A dermoscopic image of a skin lesion.
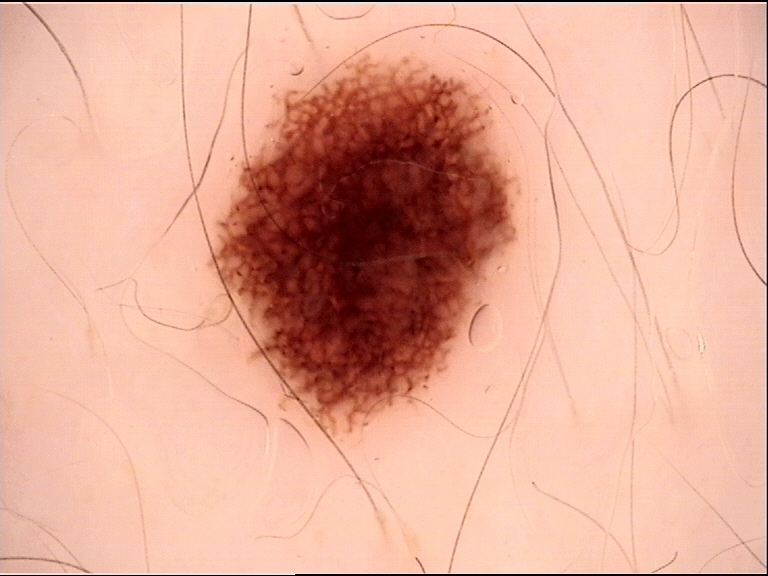diagnosis = dysplastic junctional nevus (expert consensus).